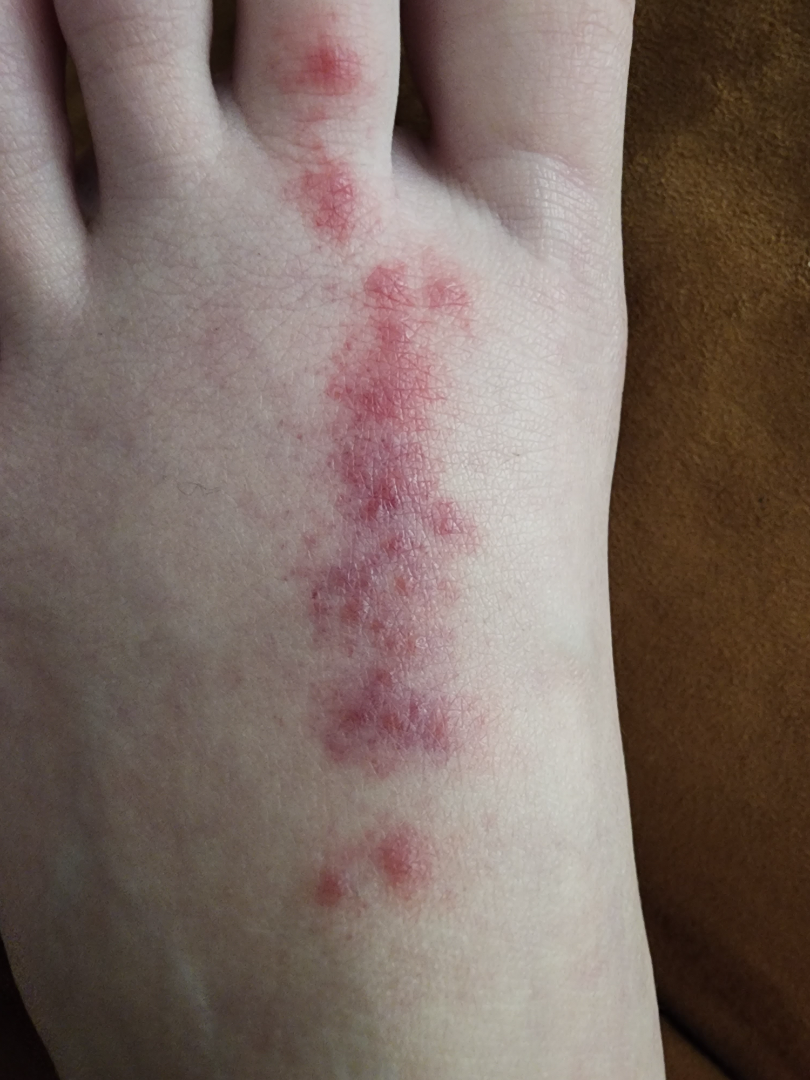Background:
This is a close-up image. Symptoms reported: itching, darkening, enlargement and bothersome appearance. The condition has been present for less than one week. Texture is reported as raised or bumpy. No associated systemic symptoms reported. The top or side of the foot is involved. Female patient, age 18–29. The patient considered this a rash.
Findings:
On teledermatology review, most likely Allergic Contact Dermatitis; also on the differential is Insect Bite; less probable is Herpes Zoster; less likely is Cutaneous larva migrans.